The contributor reports the condition has been present for one to three months · texture is reported as raised or bumpy · the patient considered this a rash · the arm and leg are involved · no constitutional symptoms were reported · the photo was captured at an angle · symptoms reported: itching, enlargement and bothersome appearance · female patient, age 18–29: 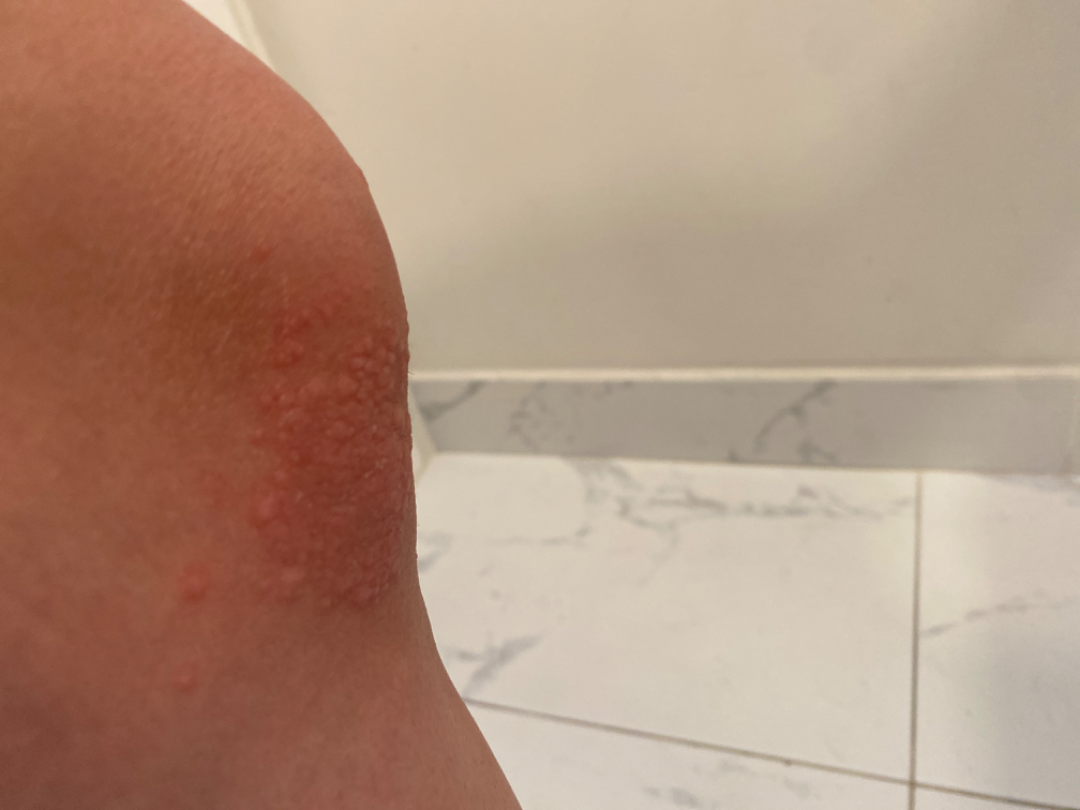Findings:
– dermatologist impression · three independent reviewers: the leading consideration is Allergic Contact Dermatitis; possibly Herpes Zoster; the differential also includes Herpes Simplex